Located on the leg, the patient is a female aged 50–59, the photo was captured at an angle.
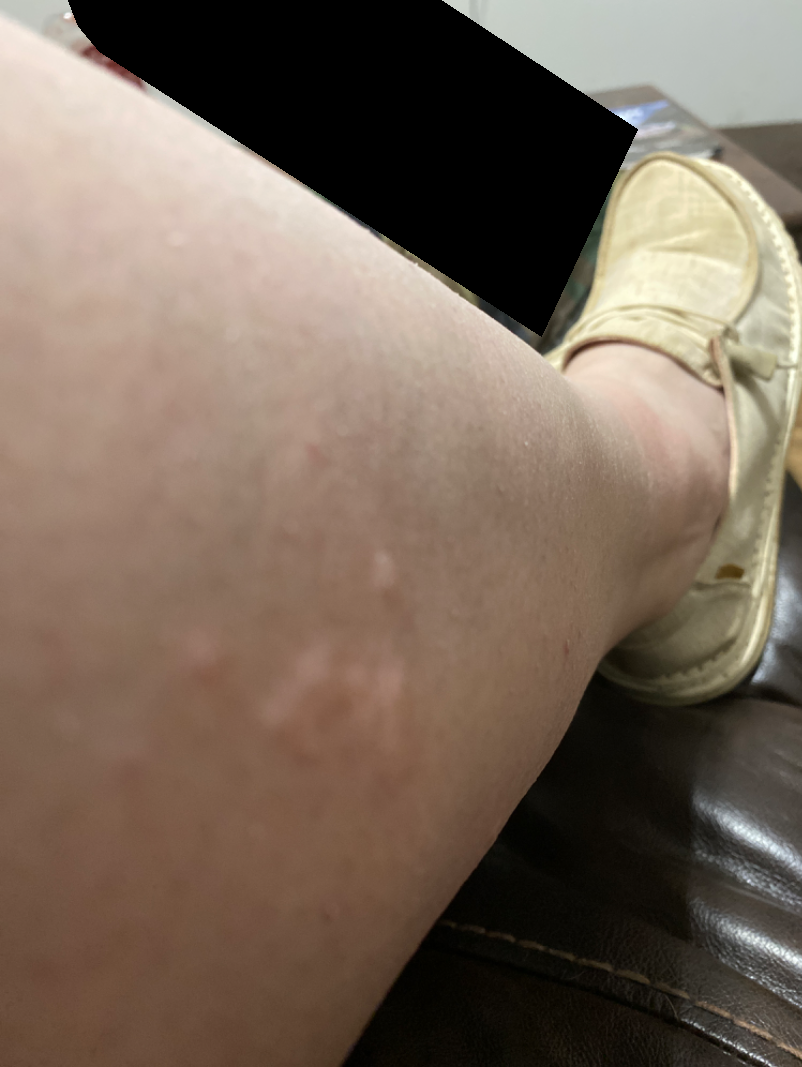No differential diagnosis could be assigned on photographic review.
The patient reported no systemic symptoms.
Reported duration is about one day.
Texture is reported as raised or bumpy.
The patient indicates itching.
Fitzpatrick phototype IV; lay graders estimated Monk Skin Tone 2 or 4 (two reviewer pools disagreed).